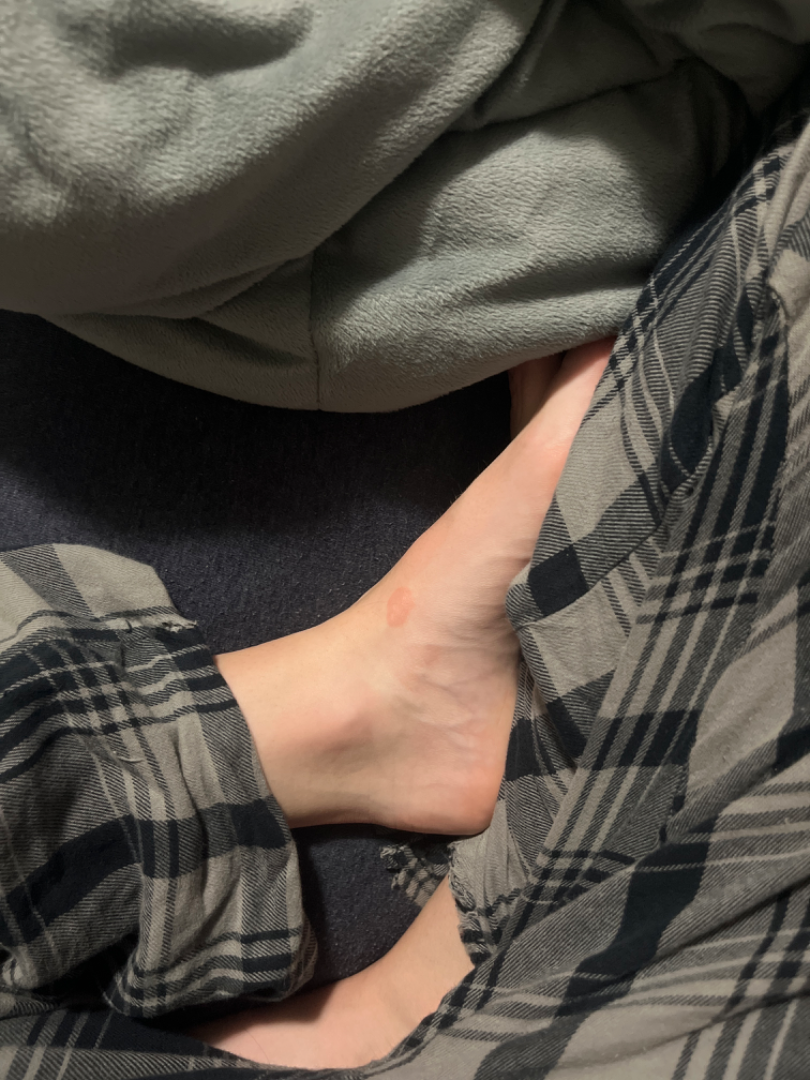Impression:
Tinea (considered); Eczema (considered); Allergic Contact Dermatitis (considered).